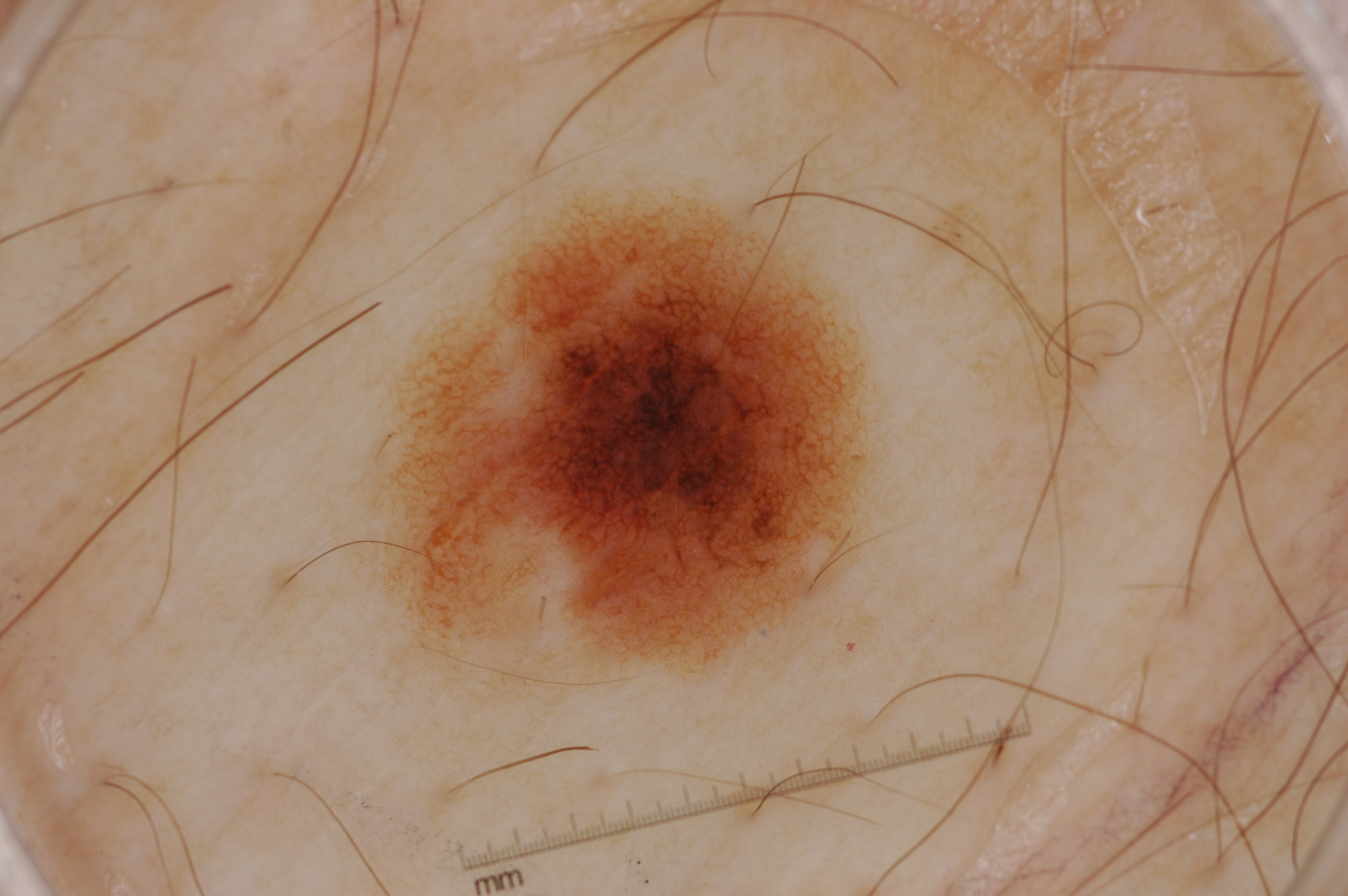image:
  modality: dermoscopy
patient:
  sex: female
  age_approx: 30
lesion_location:
  bbox_xyxy:
    - 327
    - 157
    - 919
    - 806
dermoscopic_features:
  present:
    - pigment network
  absent:
    - negative network
    - milia-like cysts
    - streaks
lesion_extent: moderate
diagnosis:
  name: melanocytic nevus
  malignancy: benign
  lineage: melanocytic
  provenance: clinical